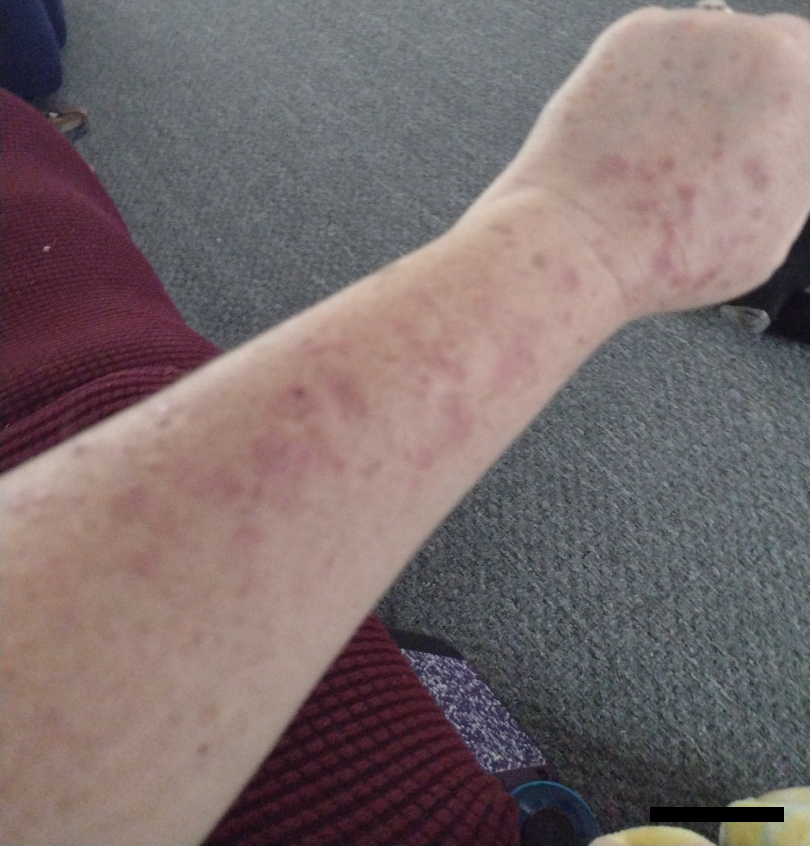Review:
No differential diagnosis could be assigned on photographic review.